Dermoscopy of a skin lesion. A male patient: 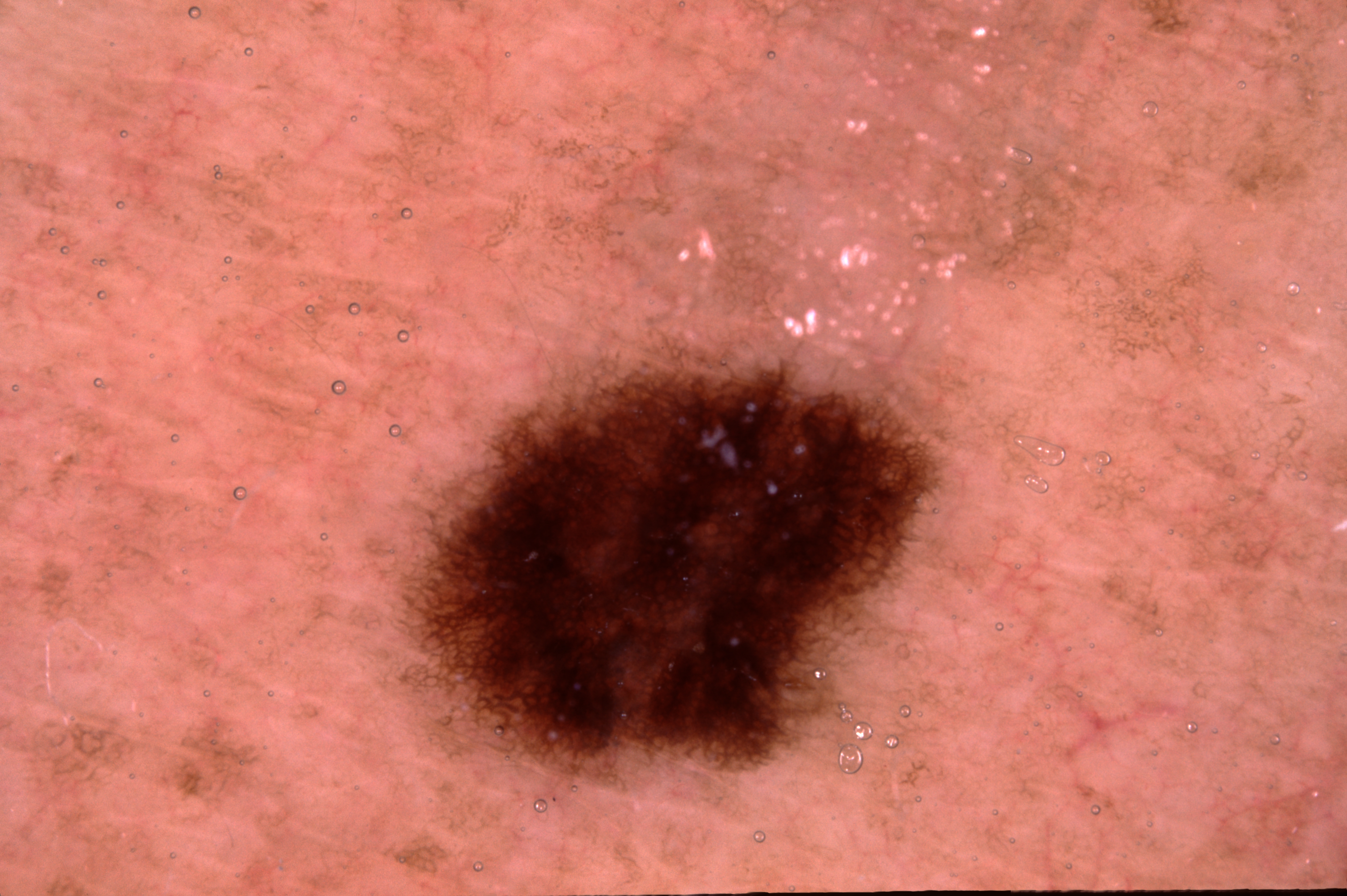dermoscopic features = pigment network; absent: milia-like cysts, streaks, and negative network | location = 398 338 943 790 | lesion extent = ~14% of the field | diagnosis = a melanocytic nevus, a benign skin lesion.